Self-categorized by the patient as a rash; the subject is 18–29, female; reported duration is about one day; the lesion is described as raised or bumpy; the arm is involved; the patient reports enlargement, pain and burning; close-up view: 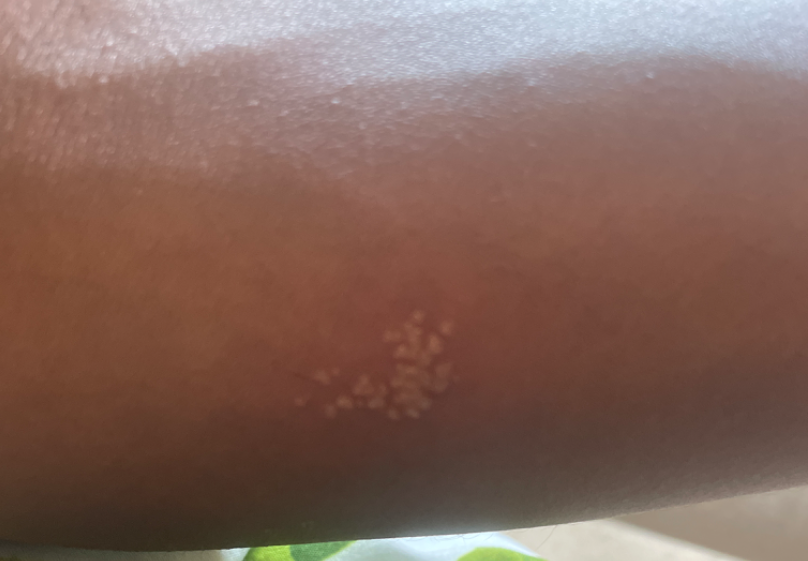The impression is Herpes Simplex.